A dermoscopic image of a skin lesion.
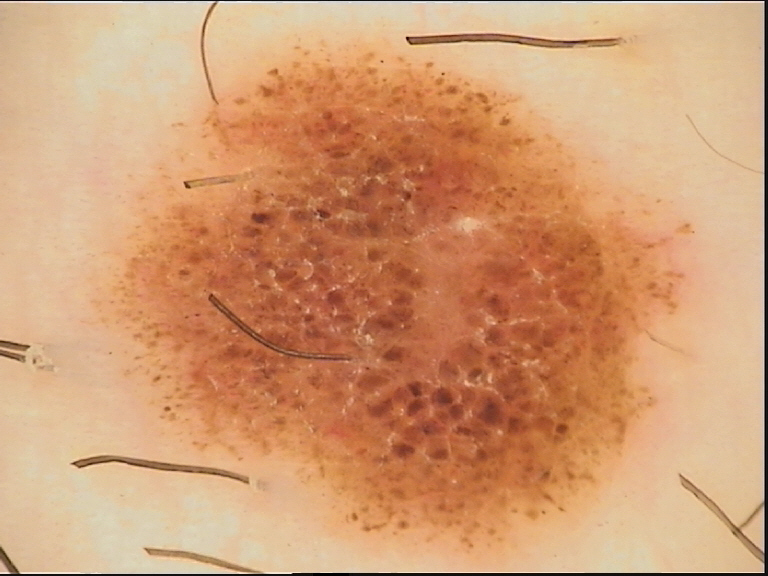Consistent with a compound nevus.